A skin lesion imaged with a dermatoscope.
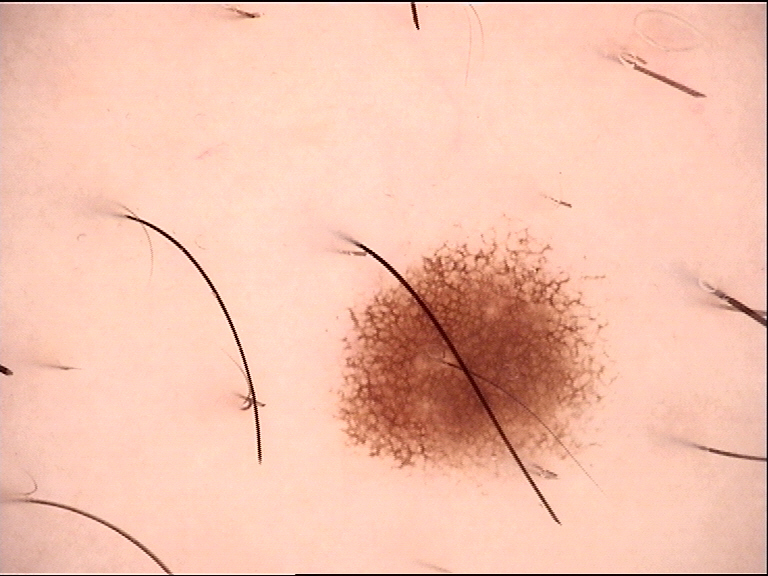The diagnosis was a benign lesion — a dysplastic junctional nevus.